Dermoscopy of a skin lesion.
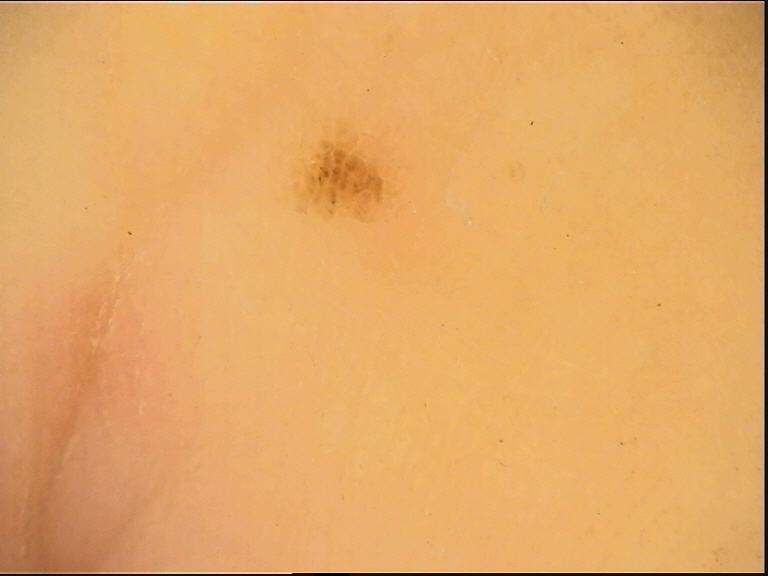diagnostic label: acral junctional nevus (expert consensus)